A dermatoscopic image of a skin lesion.
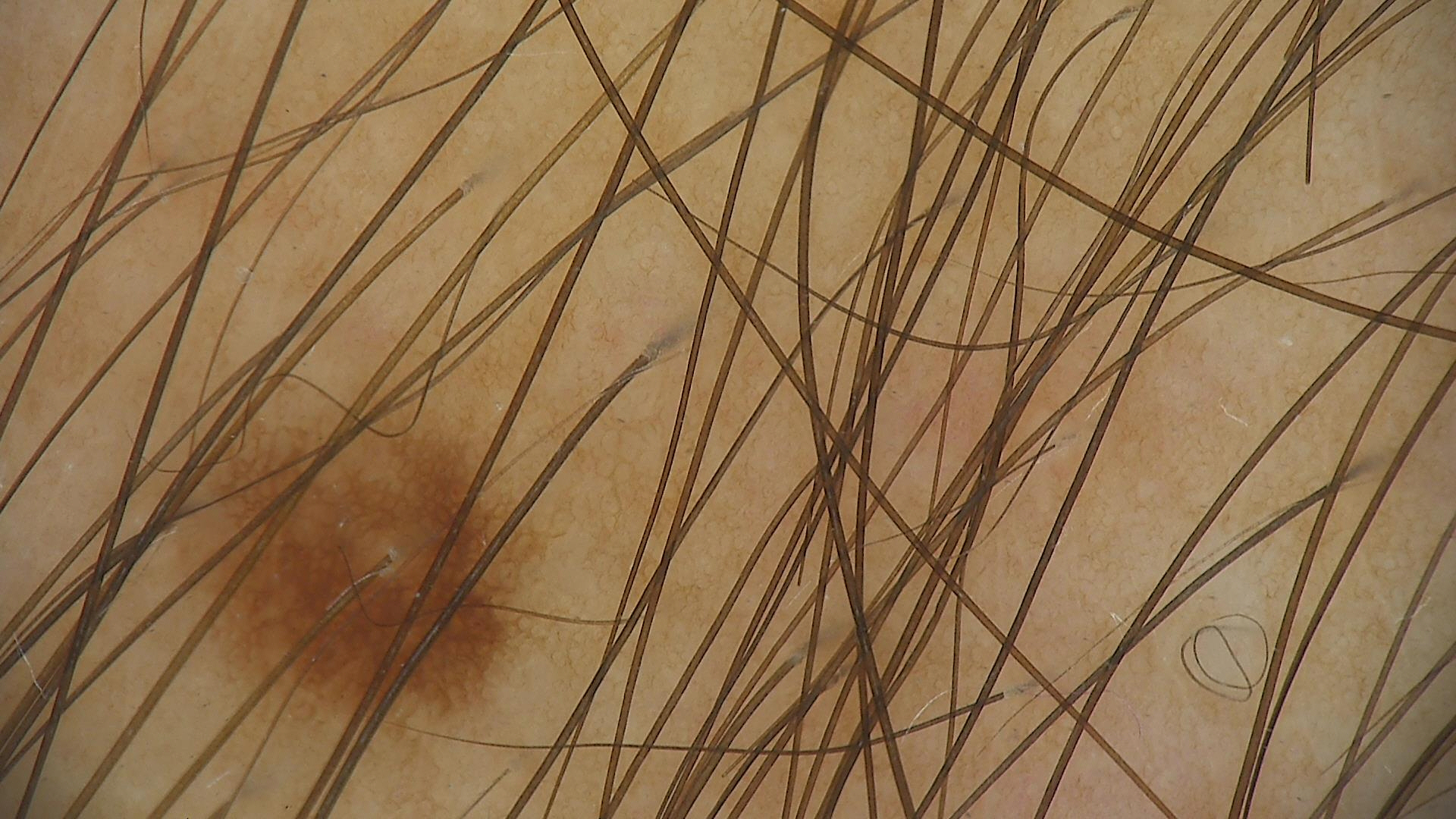{"diagnosis": {"name": "junctional nevus", "code": "jb", "malignancy": "benign", "super_class": "melanocytic", "confirmation": "expert consensus"}}